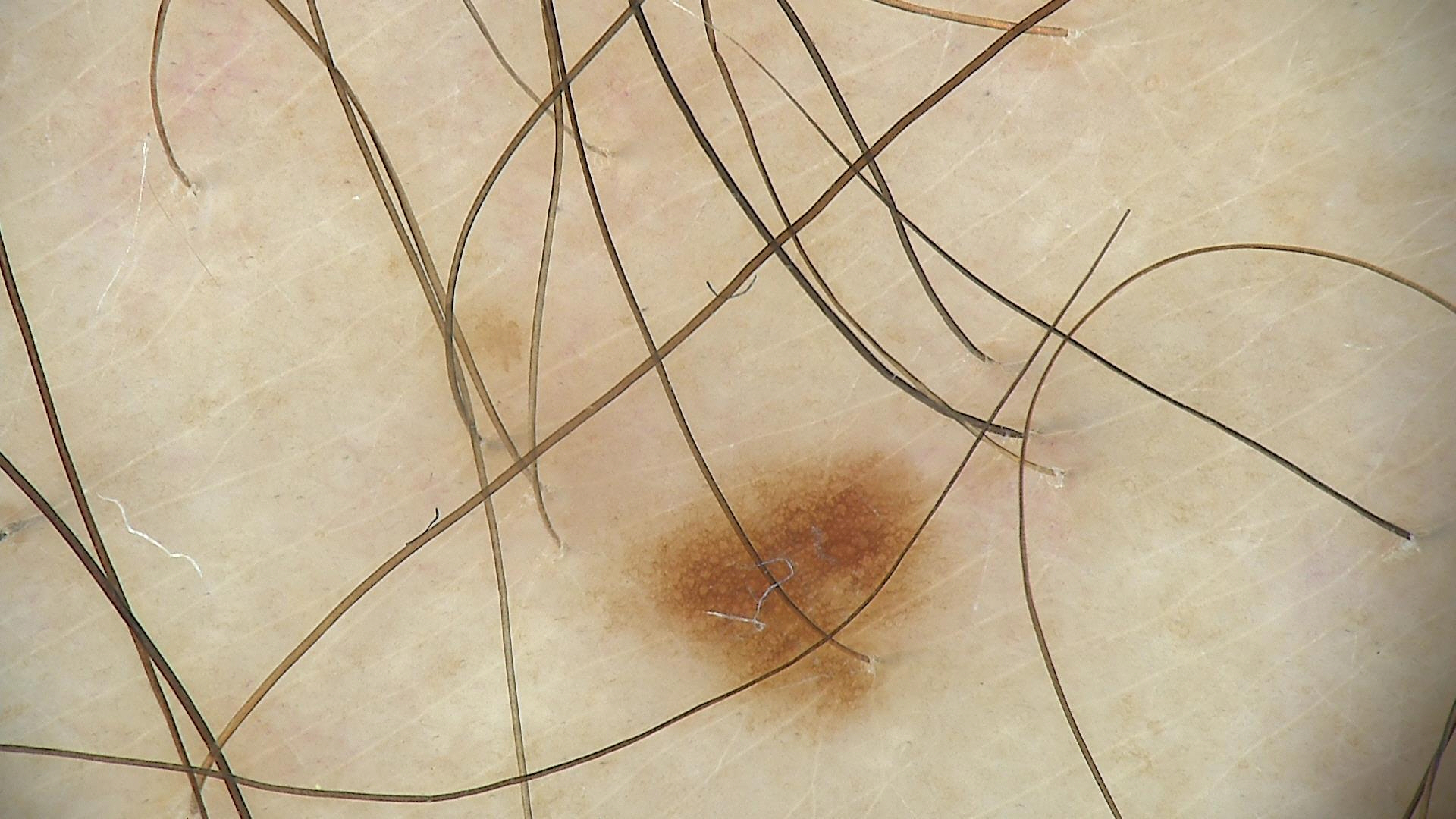Classified as a banal lesion — a junctional nevus.